The leg is involved · the photograph is a close-up of the affected area — 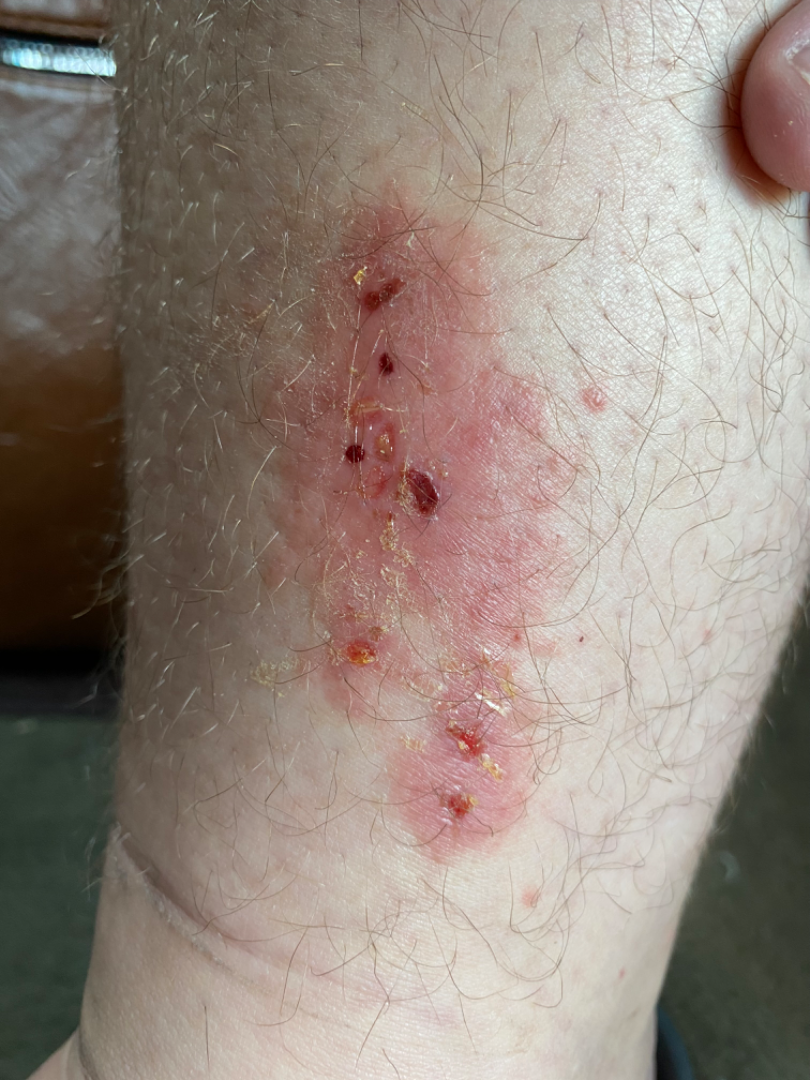Q: How does the lesion feel?
A: rough or flaky
Q: What symptoms does the patient report?
A: bothersome appearance, pain, itching and bleeding
Q: Patient's own categorization?
A: a rash
Q: What is the differential diagnosis?
A: most likely Infected eczema; also consider Eczema; also raised was Allergic Contact Dermatitis